The affected area is the arm. Reported duration is less than one week. An image taken at an angle. Self-categorized by the patient as a rash:
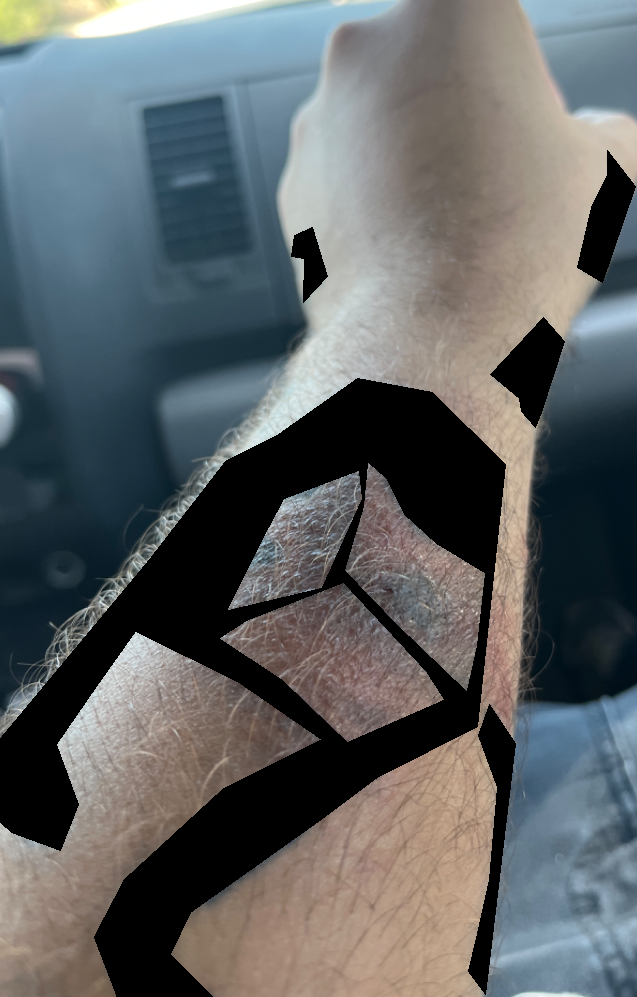| feature | finding |
|---|---|
| assessment | not assessable |